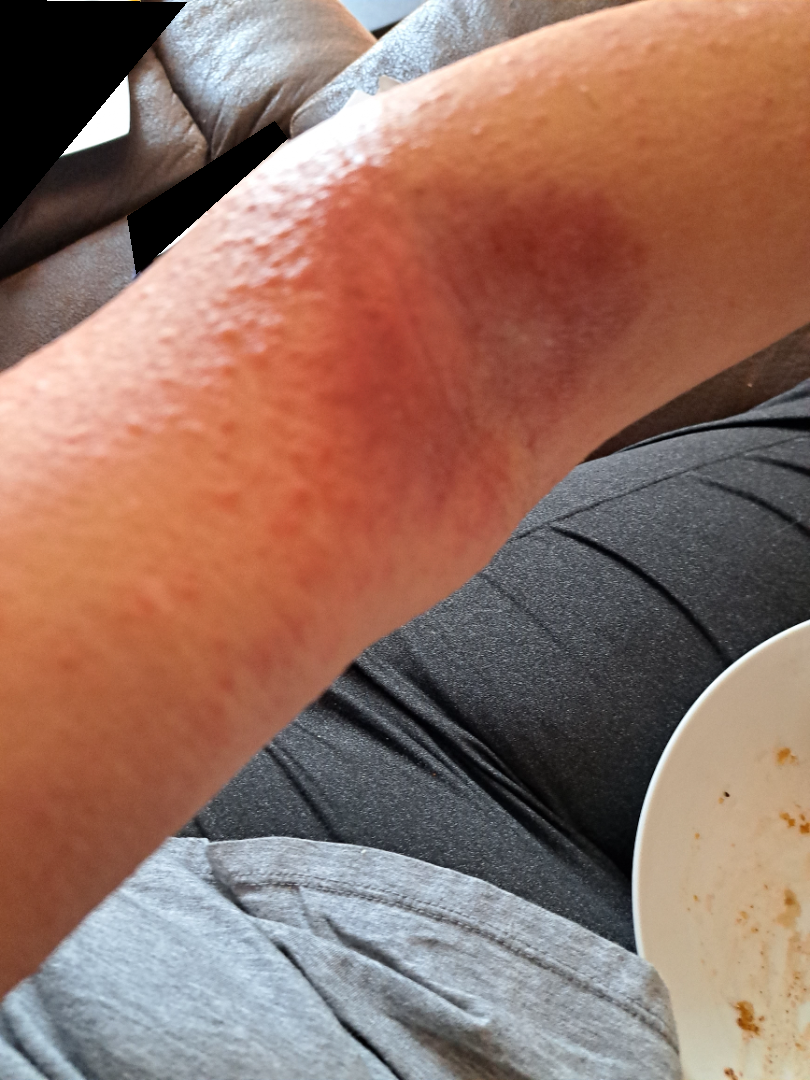assessment — not assessable
framing — at a distance